The arm is involved. The contributor notes the lesion is raised or bumpy and rough or flaky. The contributor notes the condition has been present for less than one week. This image was taken at an angle: 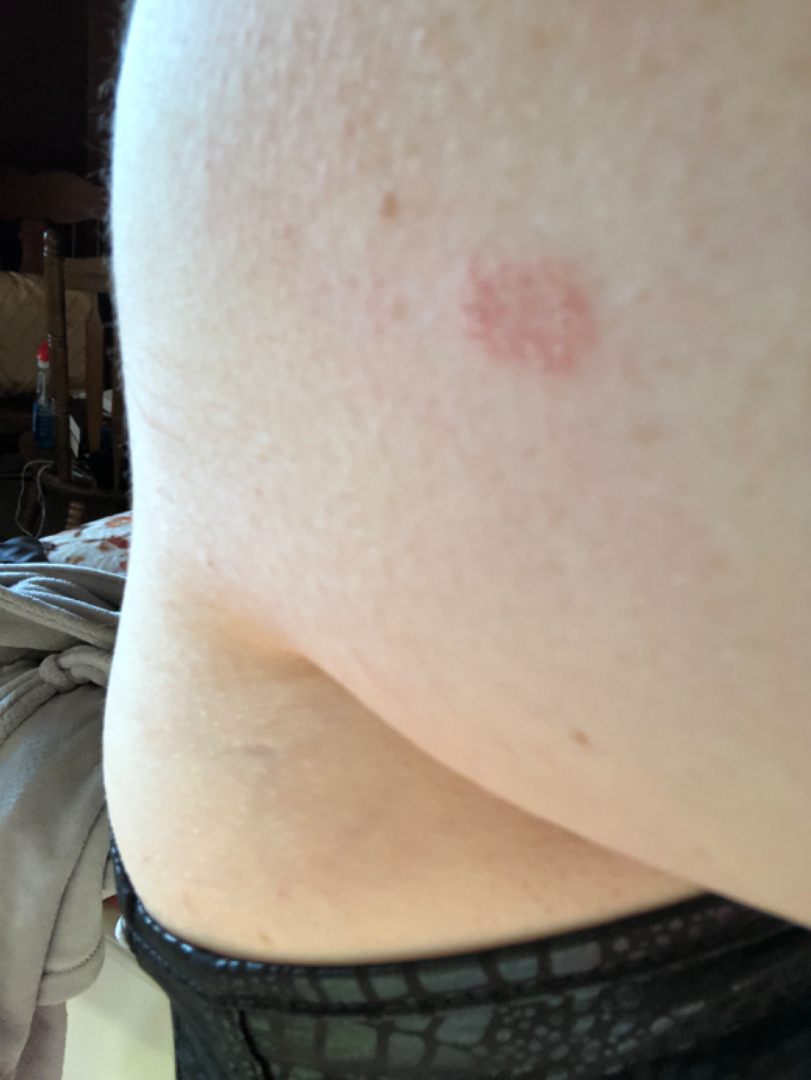- assessment · unable to determine